A female patient aged 53 to 57 · Fitzpatrick I · a contact-polarized dermoscopy image of a skin lesion · per the chart, a previous melanoma:
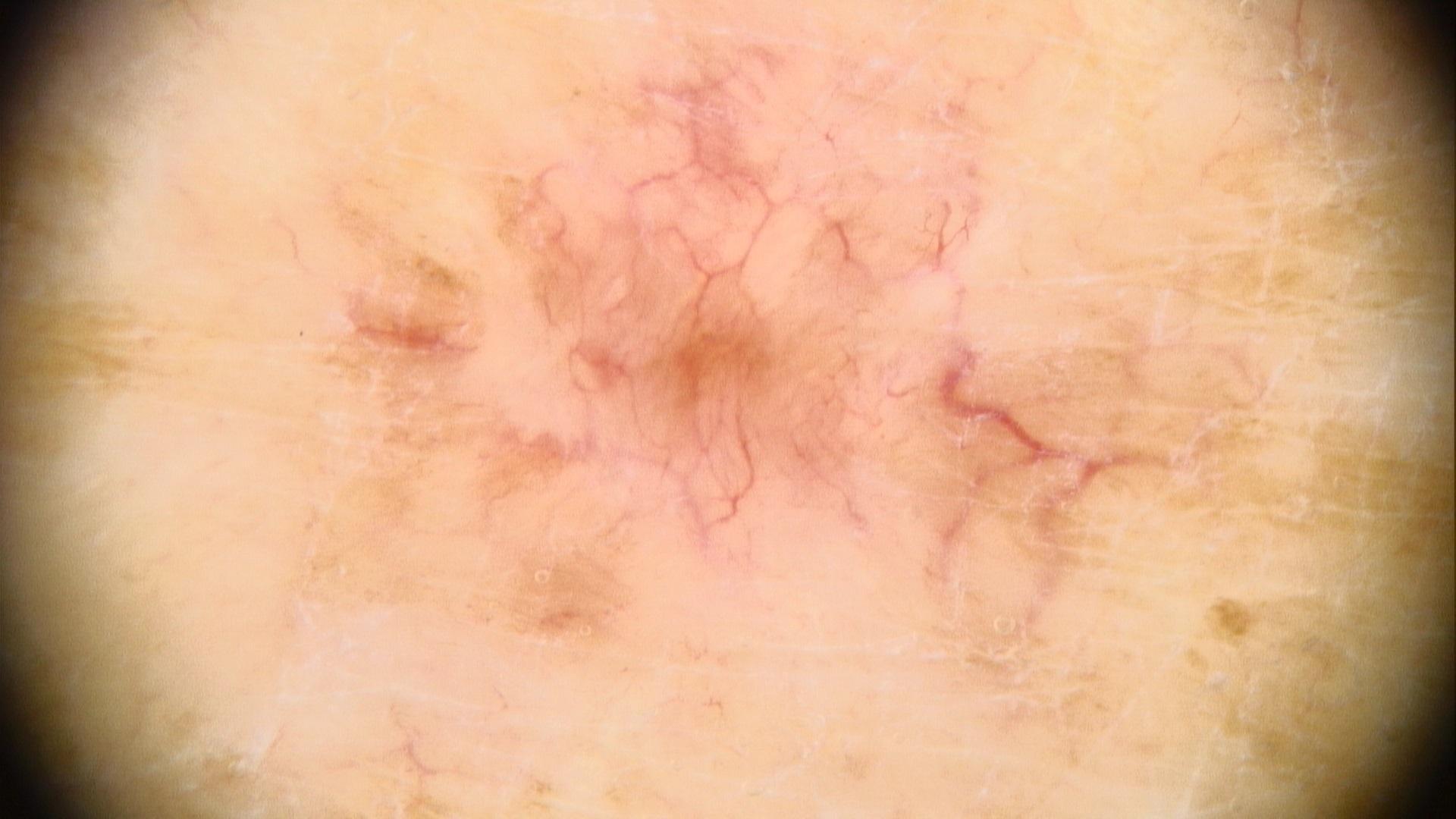Image and clinical context:
The lesion involves an upper extremity.
Pathology:
The biopsy diagnosis was a malignant, adnexal lesion — a basal cell carcinoma.